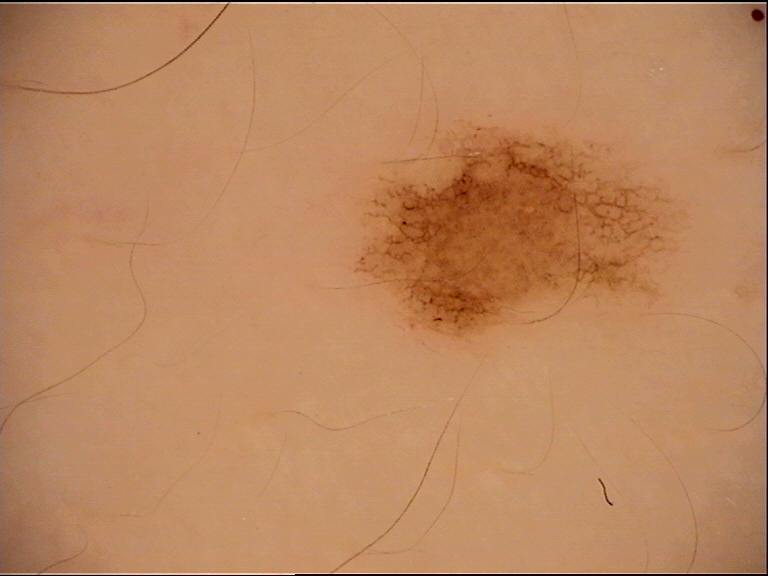Case: A dermoscopic image of a skin lesion. Impression: The diagnosis was a benign lesion — a dysplastic junctional nevus.